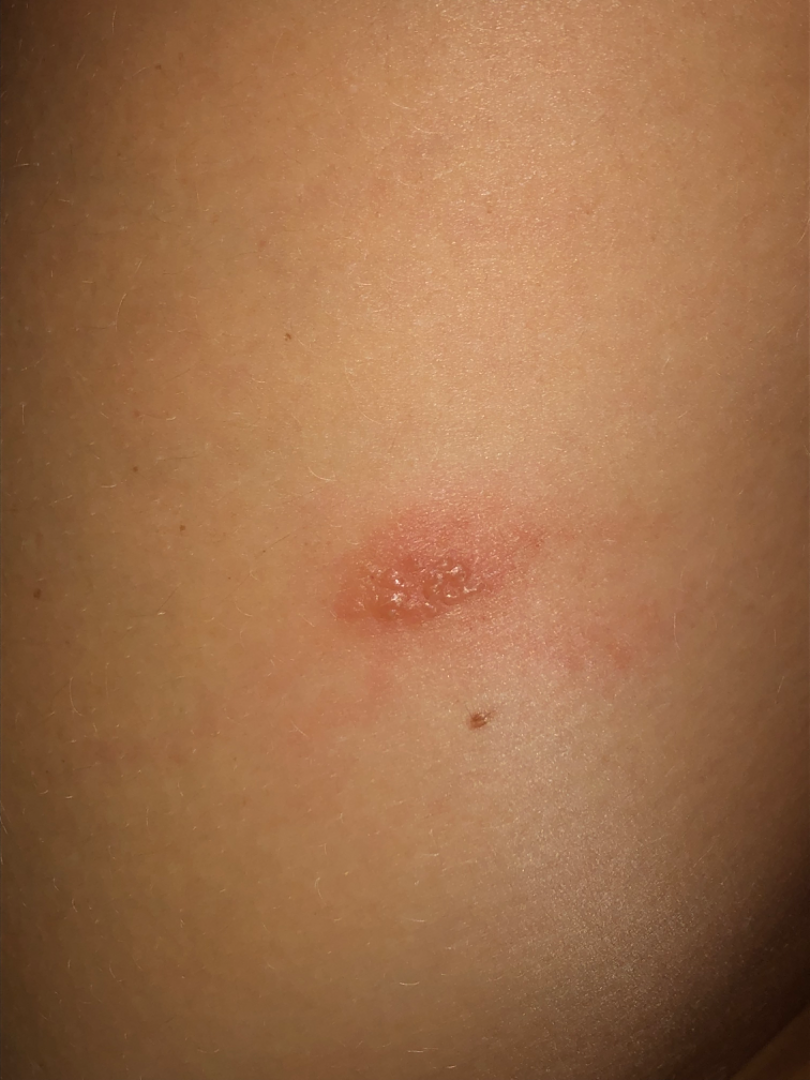– lesion texture — raised or bumpy
– self-categorized as — a rash
– constitutional symptoms — none reported
– duration — about one day
– photo taken — close-up
– contributor — female, age 40–49
– affected area — leg
– differential — Allergic Contact Dermatitis, Insect Bite and Herpes Simplex were considered with similar weight